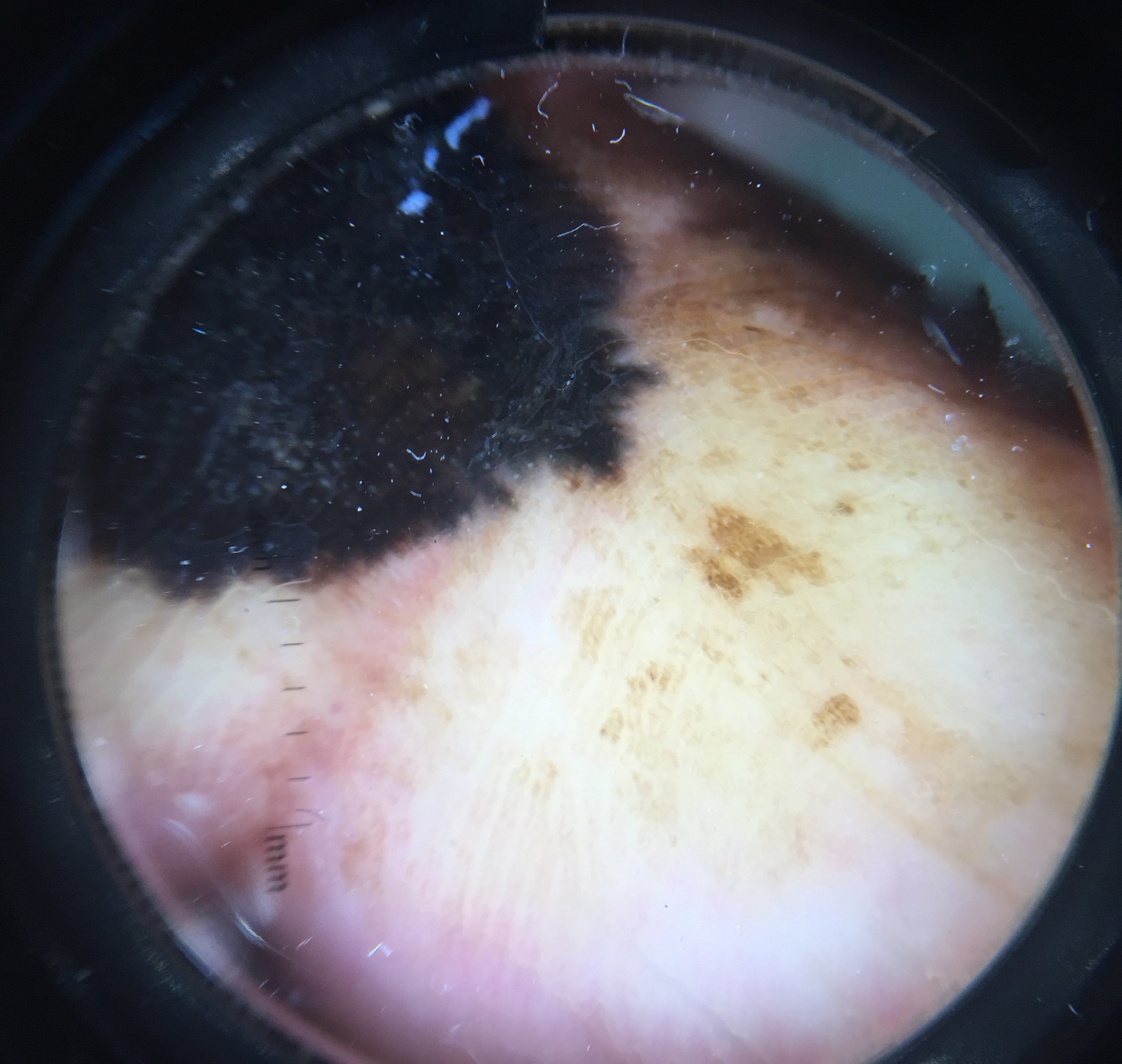Biopsy-confirmed as an acral lentiginous melanoma.